Dermoscopy of a skin lesion: 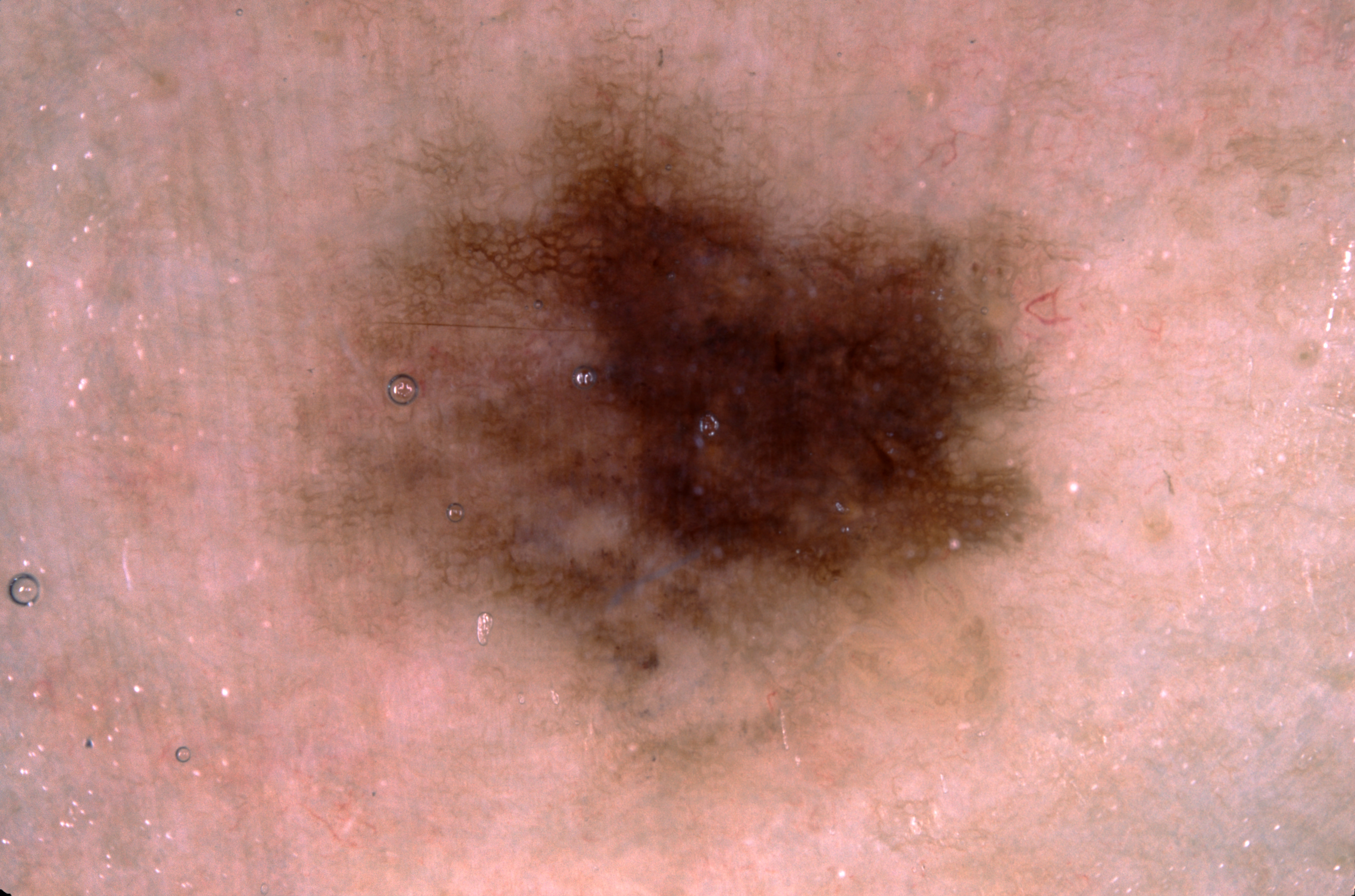Q: Where is the lesion in the image?
A: left=262, top=0, right=1074, bottom=789
Q: What is the diagnosis?
A: a melanocytic nevus